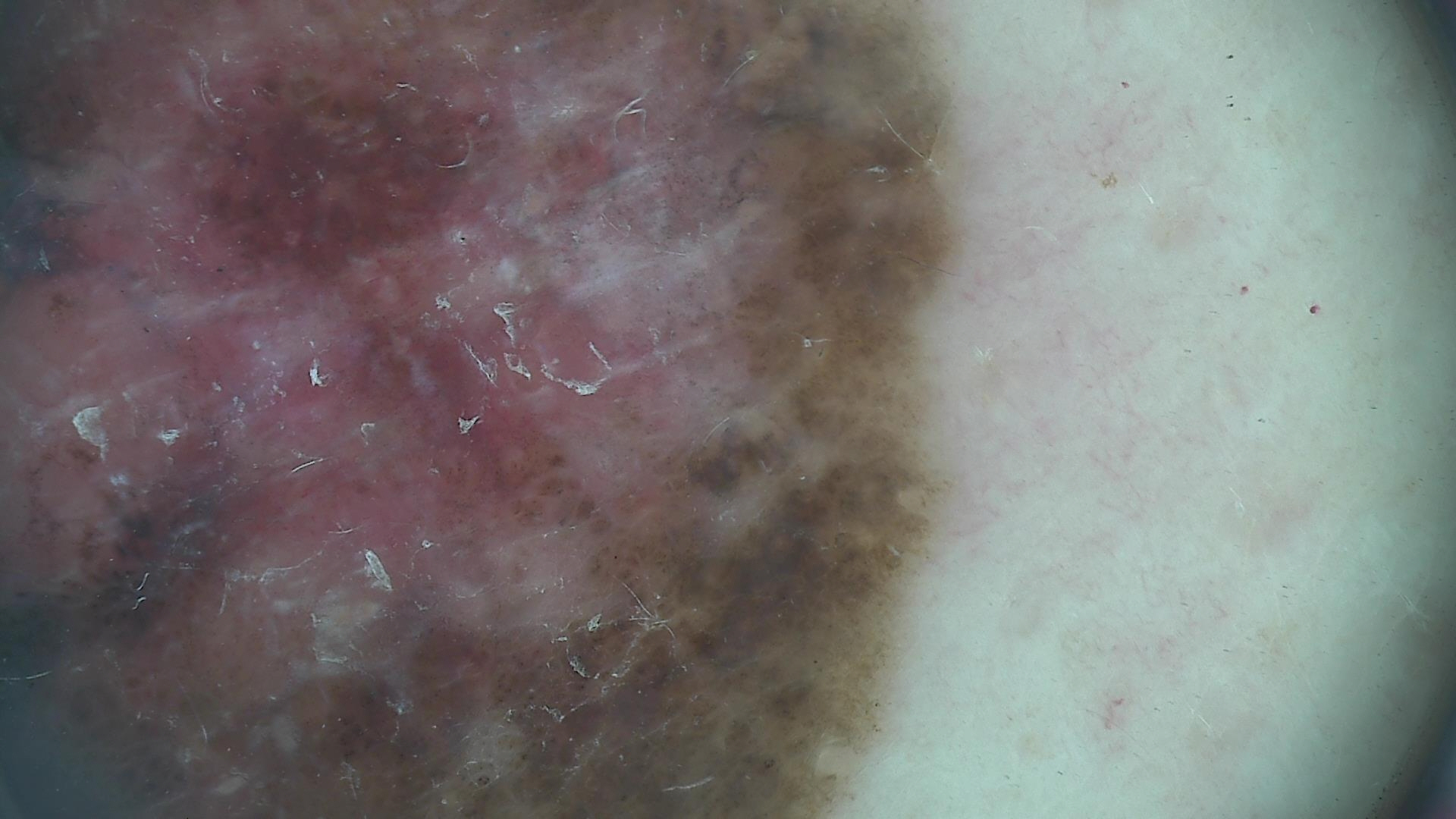Pathology: Biopsy-confirmed as a melanoma.